The lesion involves the arm. An image taken at a distance:
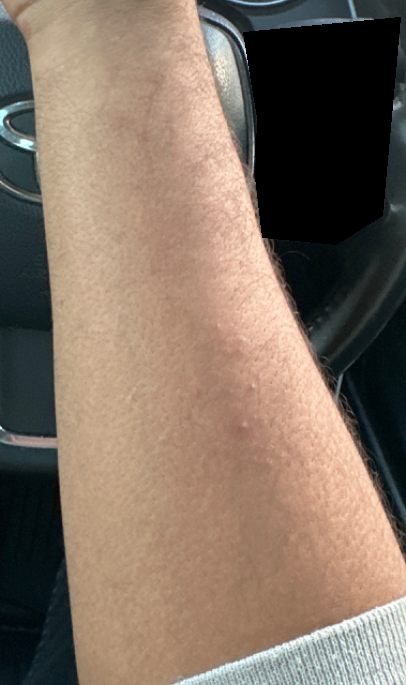| feature | finding |
|---|---|
| patient describes the issue as | acne |
| symptom duration | about one day |
| lesion texture | fluid-filled |
| lesion symptoms | bothersome appearance |
| clinical impression | the leading consideration is Eczema; the differential also includes Keratosis pilaris |